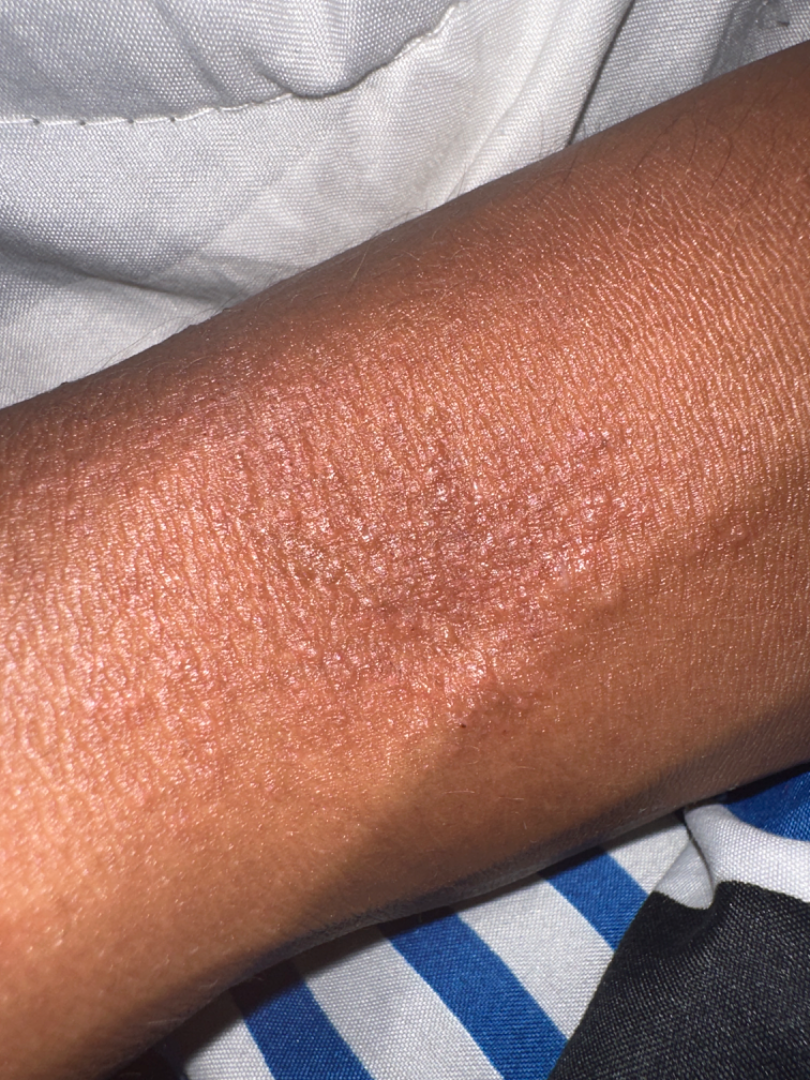The condition has been present for one to four weeks.
Texture is reported as raised or bumpy.
The photograph is a close-up of the affected area.
Fitzpatrick skin type IV.
The arm is involved.
No relevant systemic symptoms.
The contributor is 18–29, male.
On photographic review: in keeping with Eczema.